A dermoscopic image of a skin lesion.
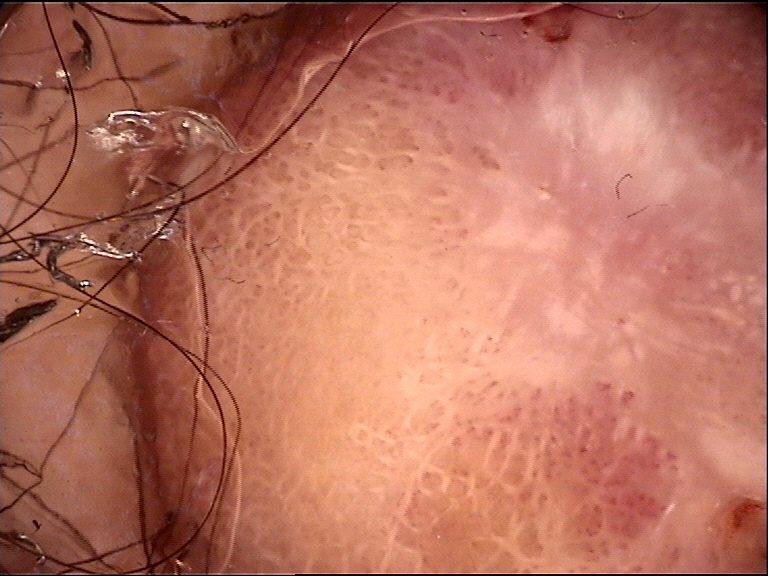Summary: The morphology is that of a fibro-histiocytic lesion. Impression: The diagnosis was a benign lesion — a dermatofibroma.